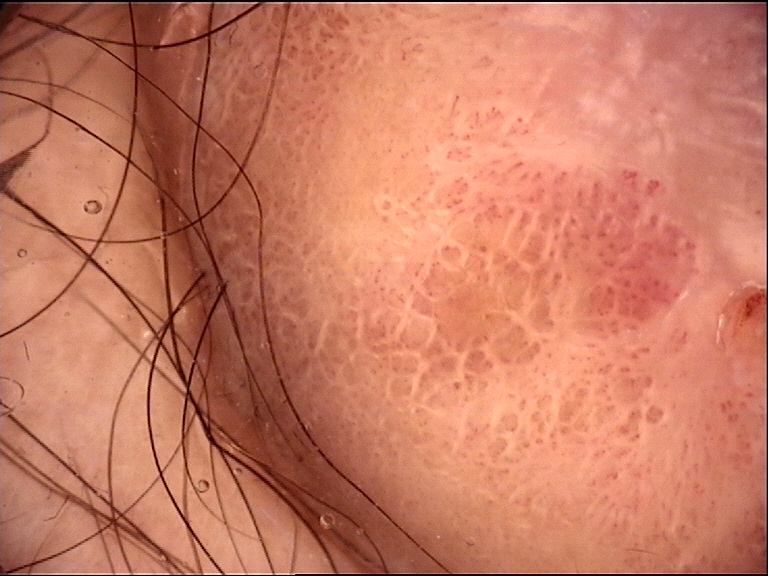Findings: The architecture is that of a fibro-histiocytic lesion. Conclusion: Diagnosed as a dermatofibroma.